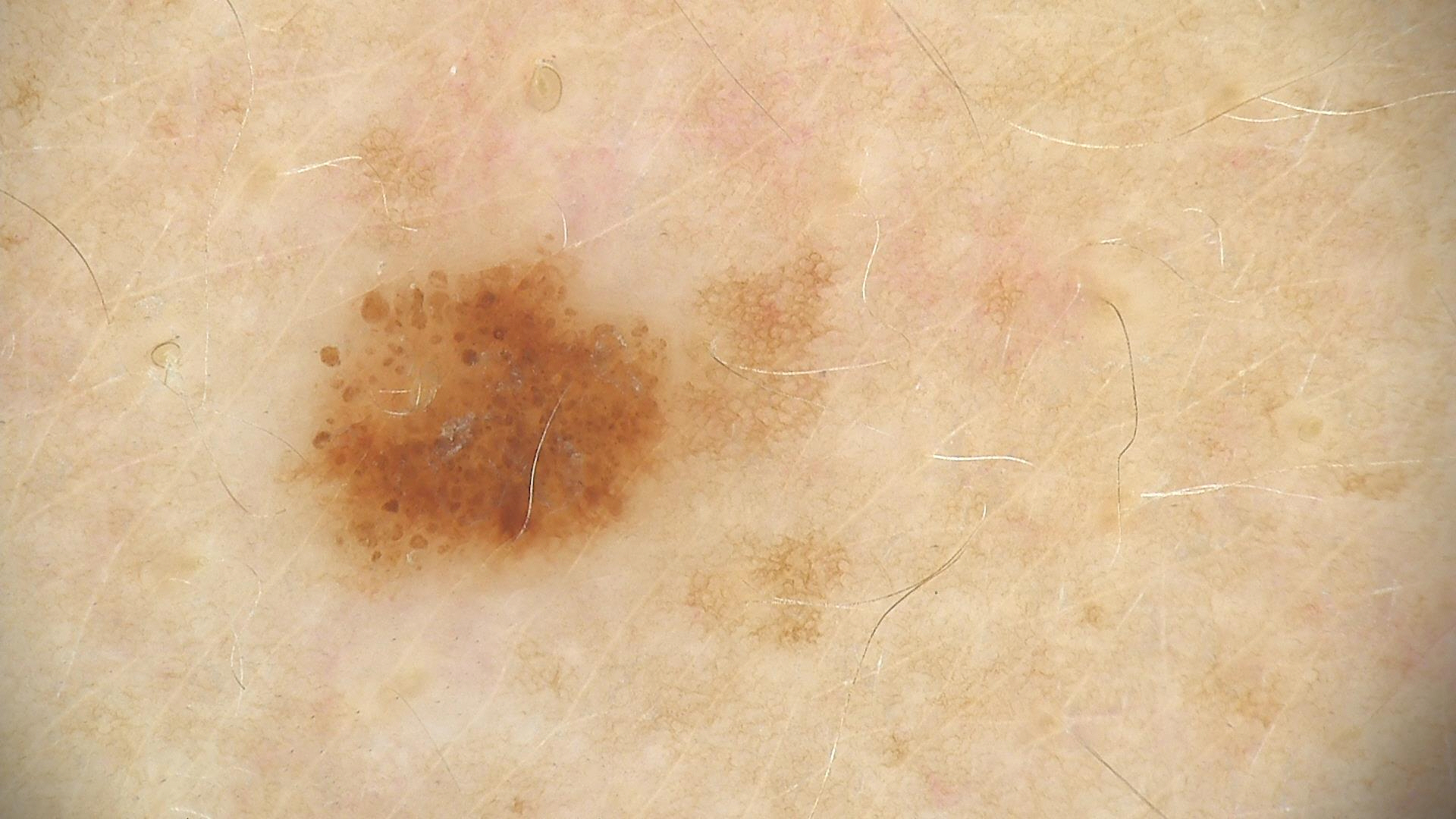Conclusion: Consistent with a dysplastic junctional nevus.